A male subject aged 88 · history notes prior malignancy (patient or family), prior skin cancer (patient or family), alcohol use, pesticide exposure, and no tobacco use · a clinical photograph showing a skin lesion · recorded as Fitzpatrick phototype II: 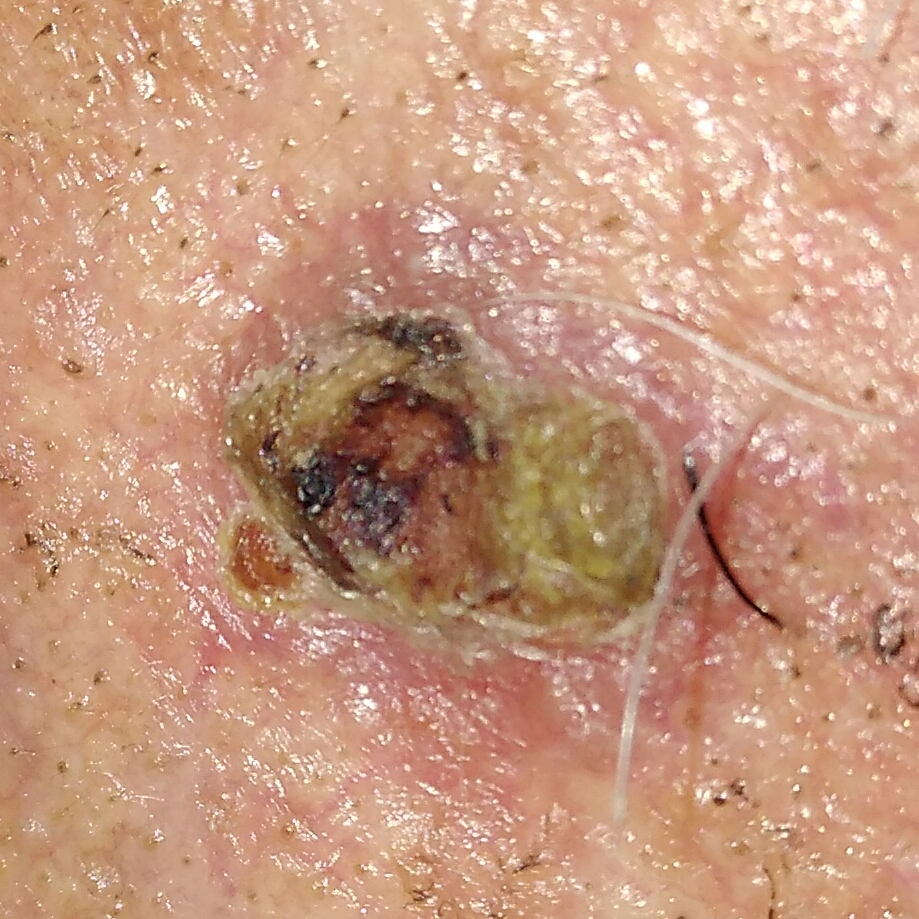{"lesion_location": "the face", "lesion_size": {"diameter_1_mm": 15.0, "diameter_2_mm": 13.0}, "symptoms": {"present": ["pain", "elevation", "bleeding", "itching"], "absent": ["growth"]}, "diagnosis": {"name": "basal cell carcinoma", "code": "BCC", "malignancy": "malignant", "confirmation": "histopathology"}}